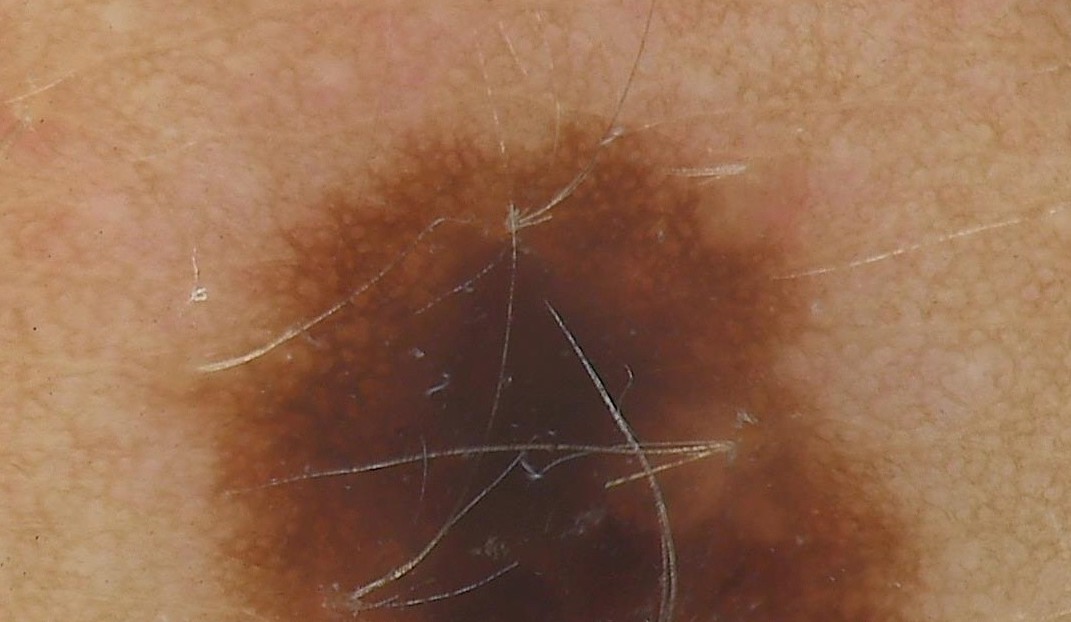Findings:
* imaging · dermoscopy
* diagnostic label · dysplastic junctional nevus (expert consensus)